A male subject 72 years of age · a clinical photo of a skin lesion taken with a smartphone: 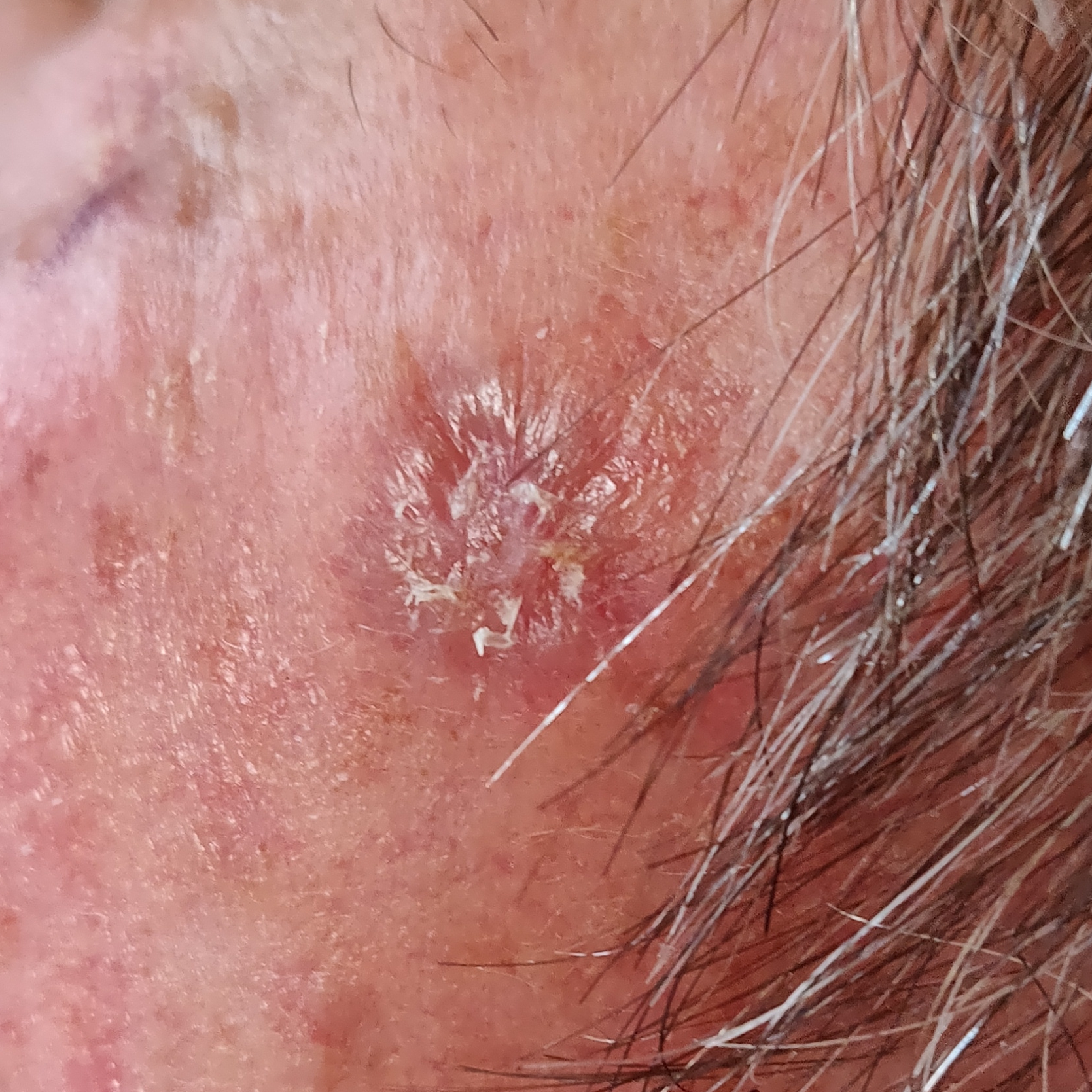Clinical context:
The lesion was found on the face. By the patient's account, the lesion is elevated, has grown, and itches.
Conclusion:
Confirmed on histopathology as a basal cell carcinoma.